Texture is reported as rough or flaky, no constitutional symptoms were reported, this image was taken at an angle, the subject is a female aged 60–69, self-categorized by the patient as a rash, the lesion involves the back of the hand and palm.
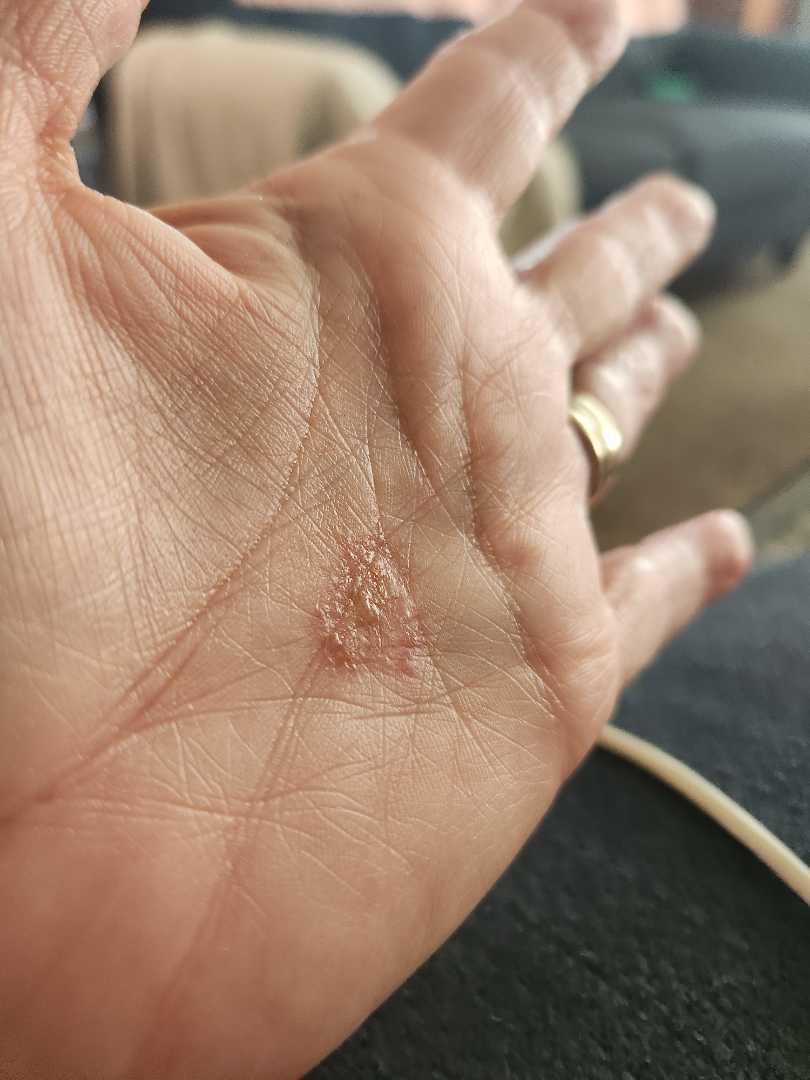On teledermatology review: the differential includes Psoriasis and Superficial wound of body region, with no clear leading consideration.